A dermatoscopic image of a skin lesion · the patient says their skin reddens with sun exposure · the patient reports a personal history of cancer, a family history of skin cancer, and a personal history of skin cancer · a female subject aged 54 — 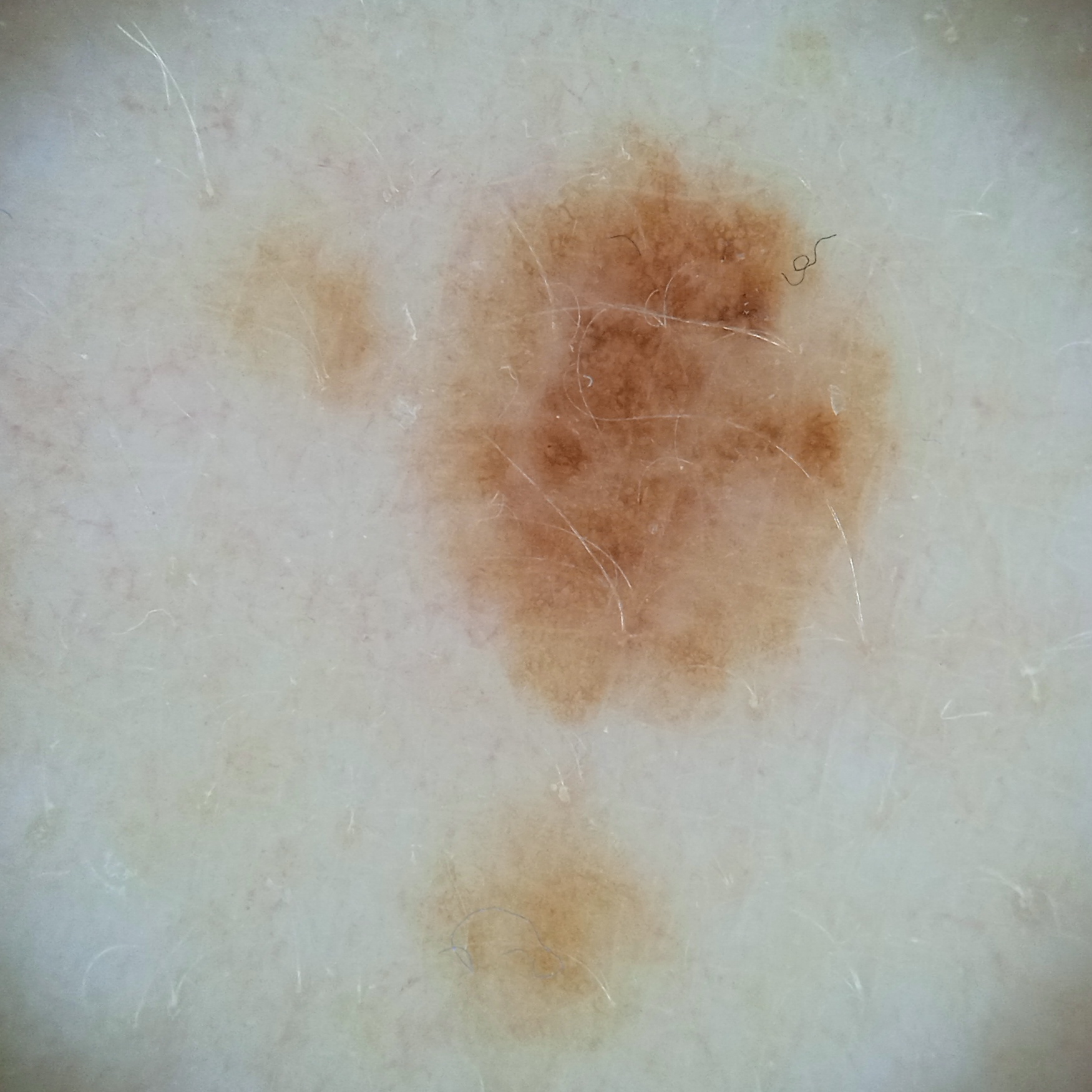body site = the back | size = 6.4 mm | diagnosis = atypical (dysplastic) nevus — dermatologist consensus.